A dermoscopic image of a skin lesion: 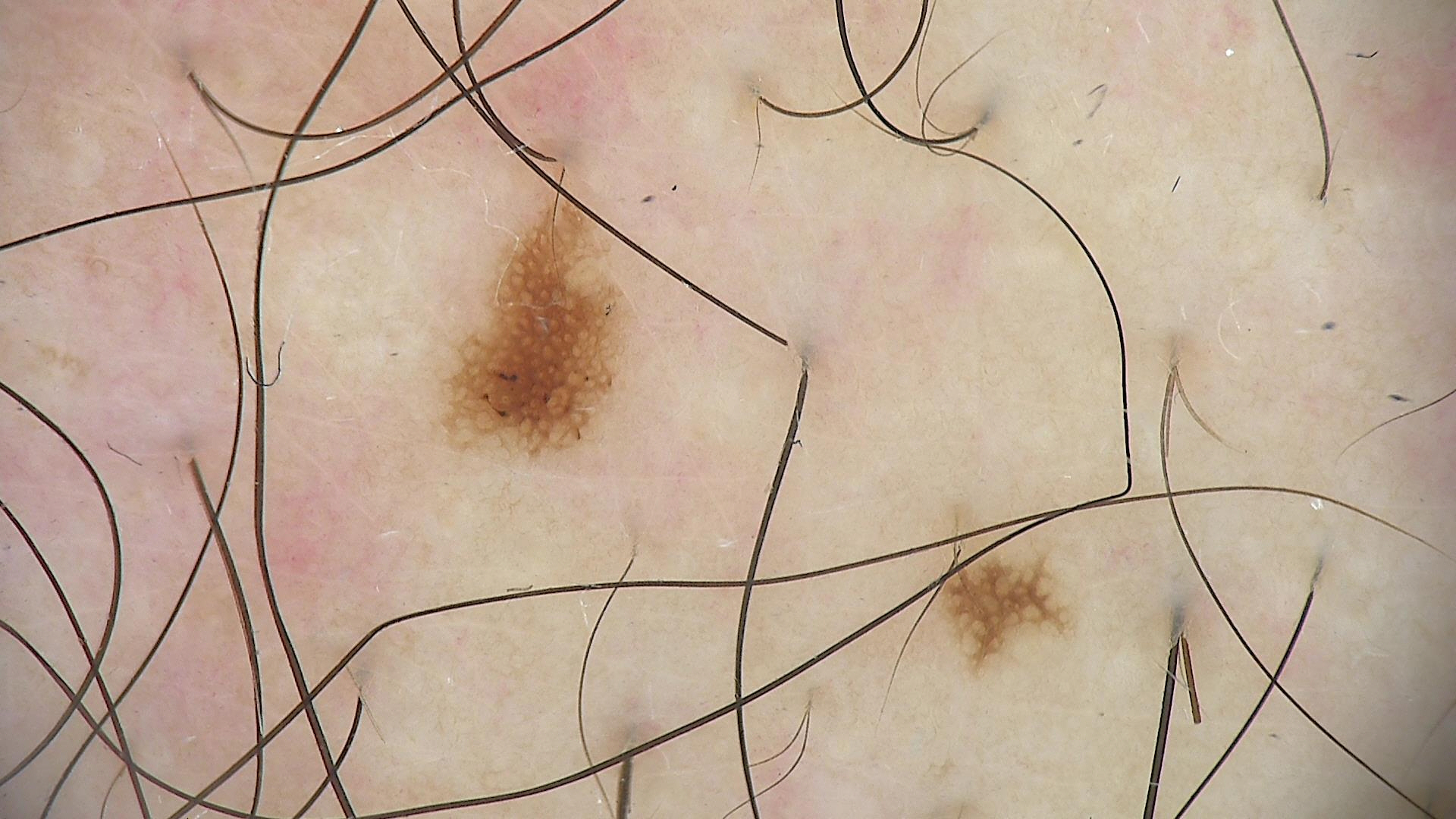{
  "diagnosis": {
    "name": "dysplastic junctional nevus",
    "code": "jd",
    "malignancy": "benign",
    "super_class": "melanocytic",
    "confirmation": "expert consensus"
  }
}